The patient is female · located on the arm, leg, head or neck and back of the hand · an image taken at an angle:
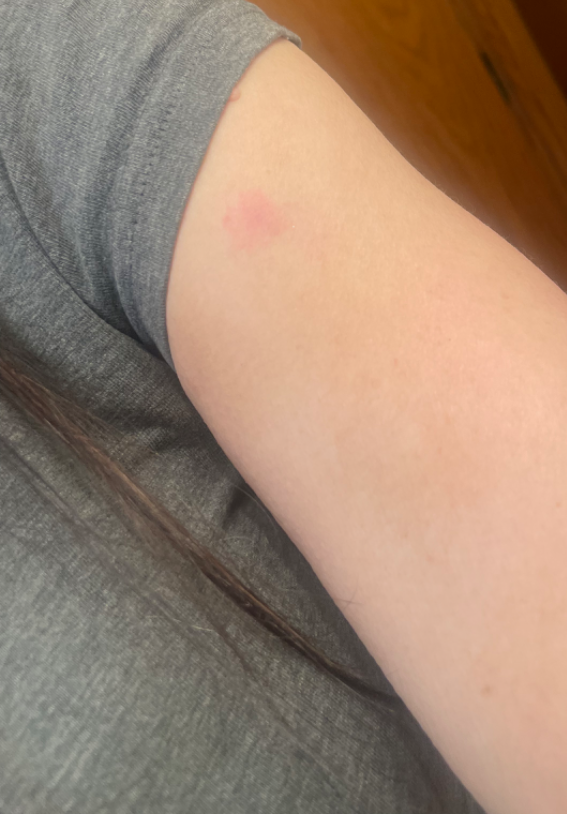Findings:
The reviewer was unable to grade this case for skin condition.